A dermoscopic photograph of a skin lesion: 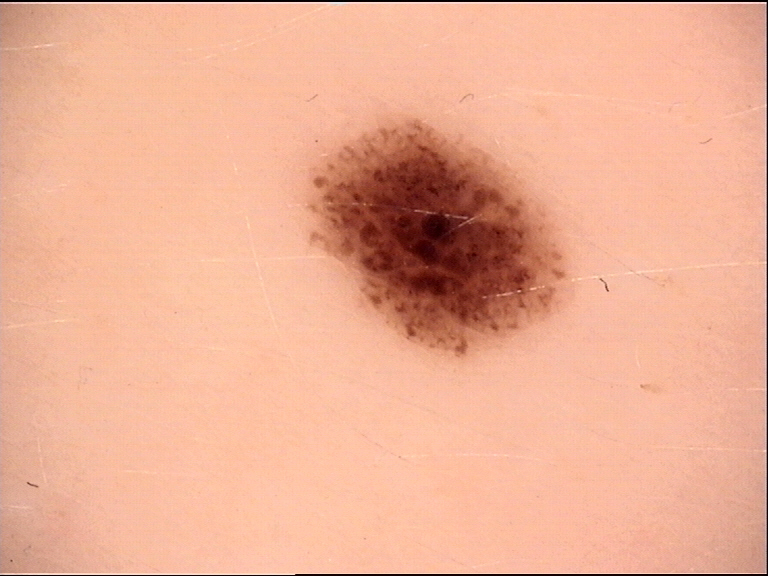Diagnosed as a benign lesion — a dysplastic compound nevus.